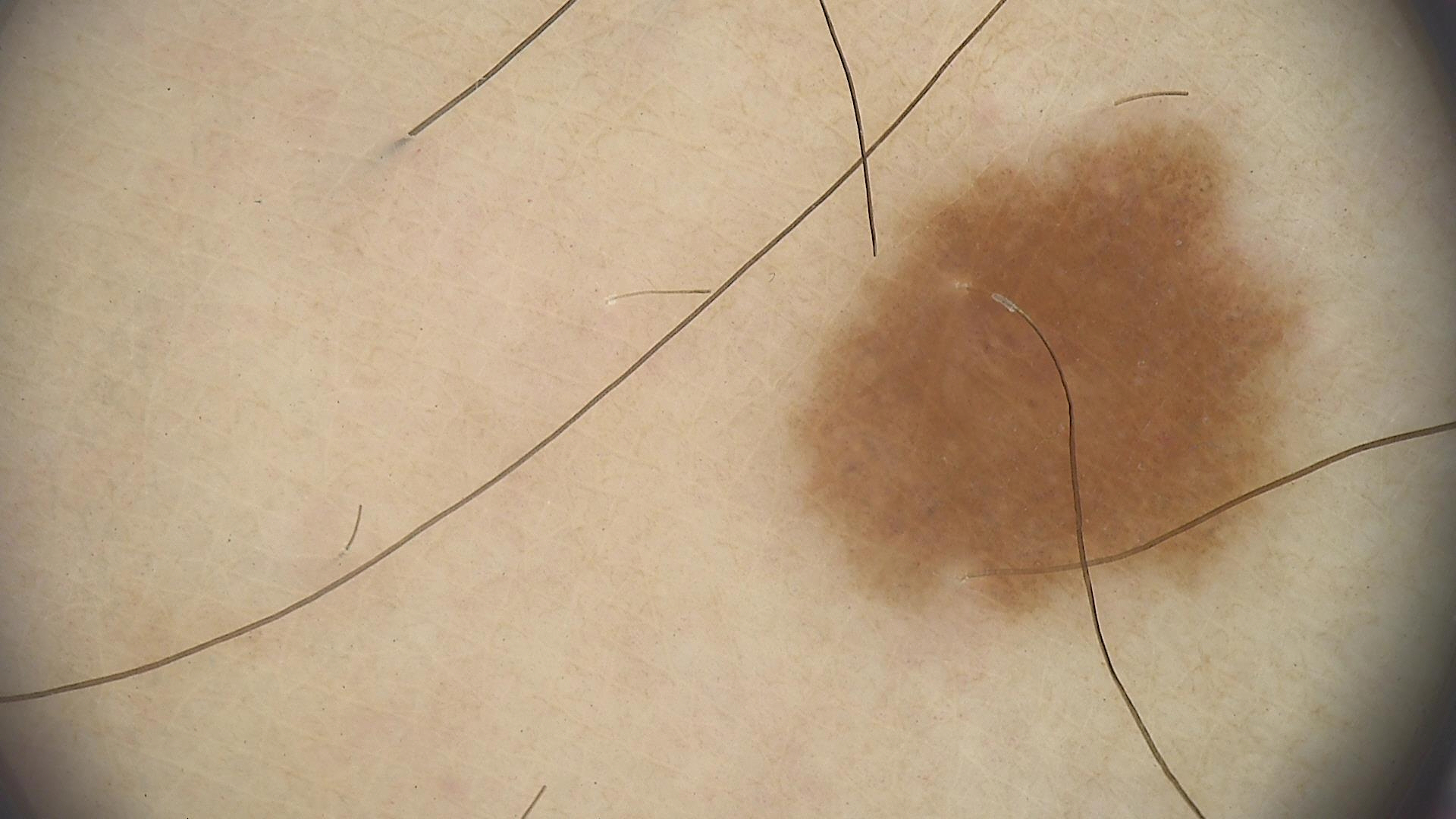{
  "diagnosis": {
    "name": "junctional nevus",
    "code": "jb",
    "malignancy": "benign",
    "super_class": "melanocytic",
    "confirmation": "expert consensus"
  }
}